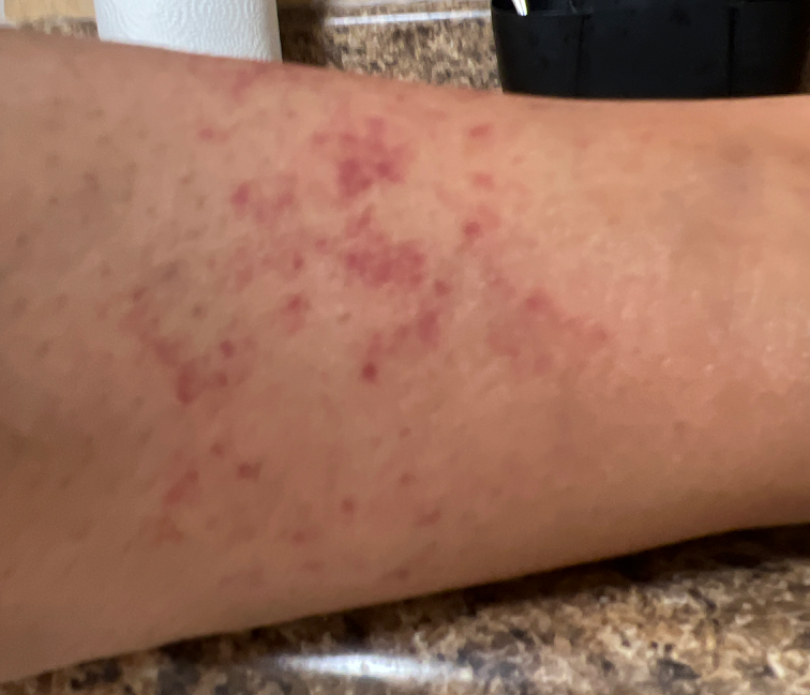Q: Could the case be diagnosed?
A: could not be assessed